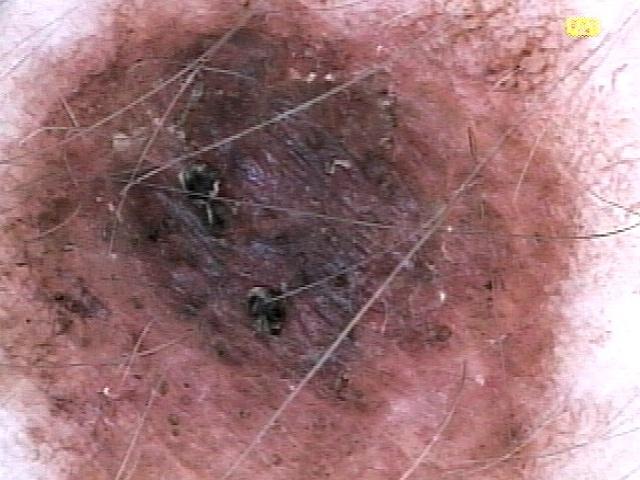The patient is Fitzpatrick phototype II. A female patient about 30 years old. Dermoscopy of a skin lesion. The lesion involves the trunk. Confirmed on histopathology as a nevus.